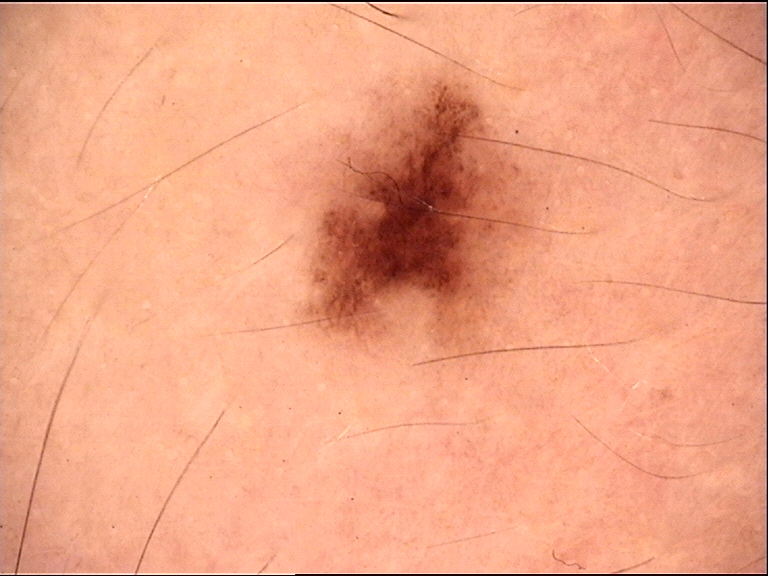The diagnostic label was a dysplastic junctional nevus.